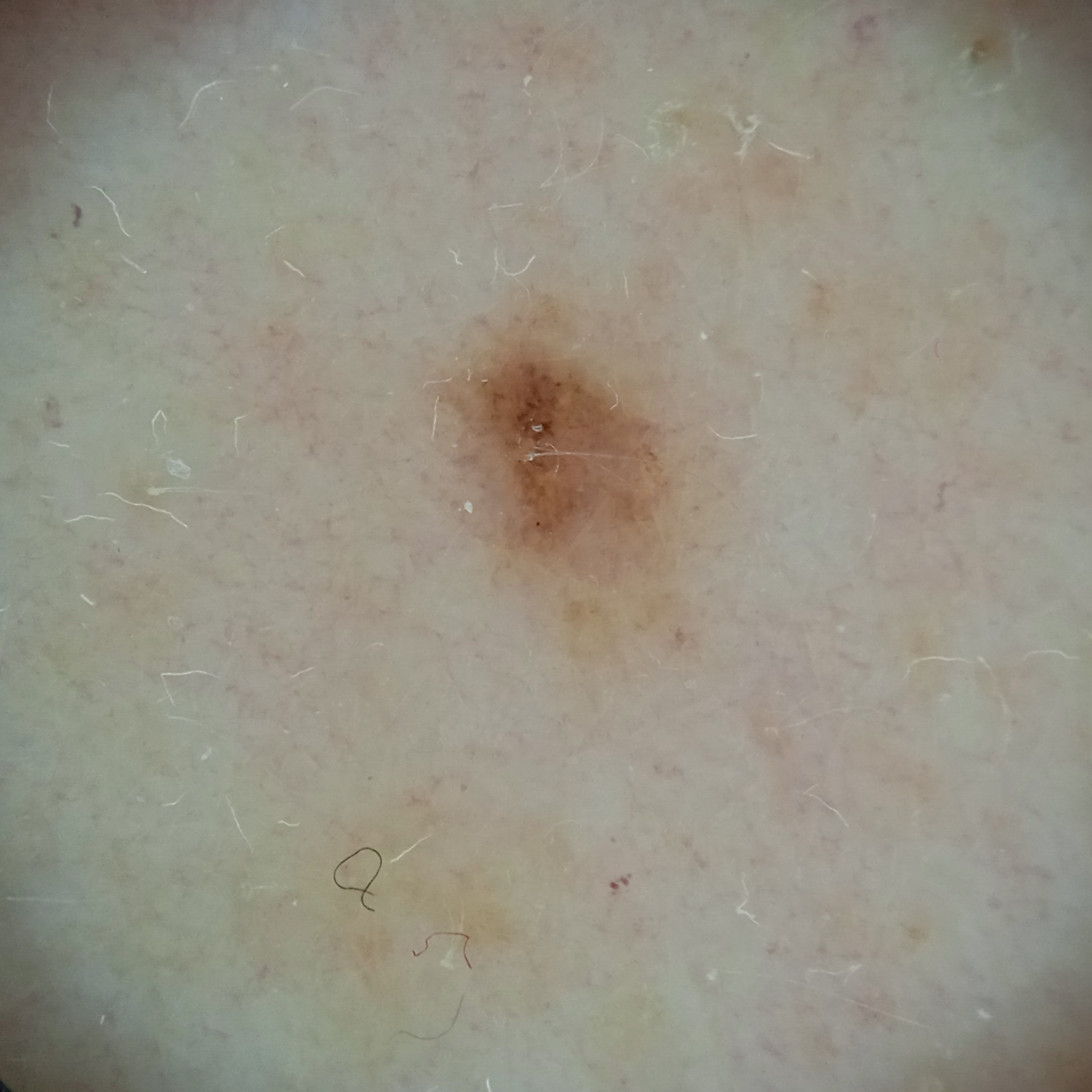A skin lesion imaged with a dermatoscope.
A female subject age 55.
Located on the back.
Measuring roughly 2.5 mm.
The diagnostic impression was a melanocytic nevus.